A dermoscopic close-up of a skin lesion.
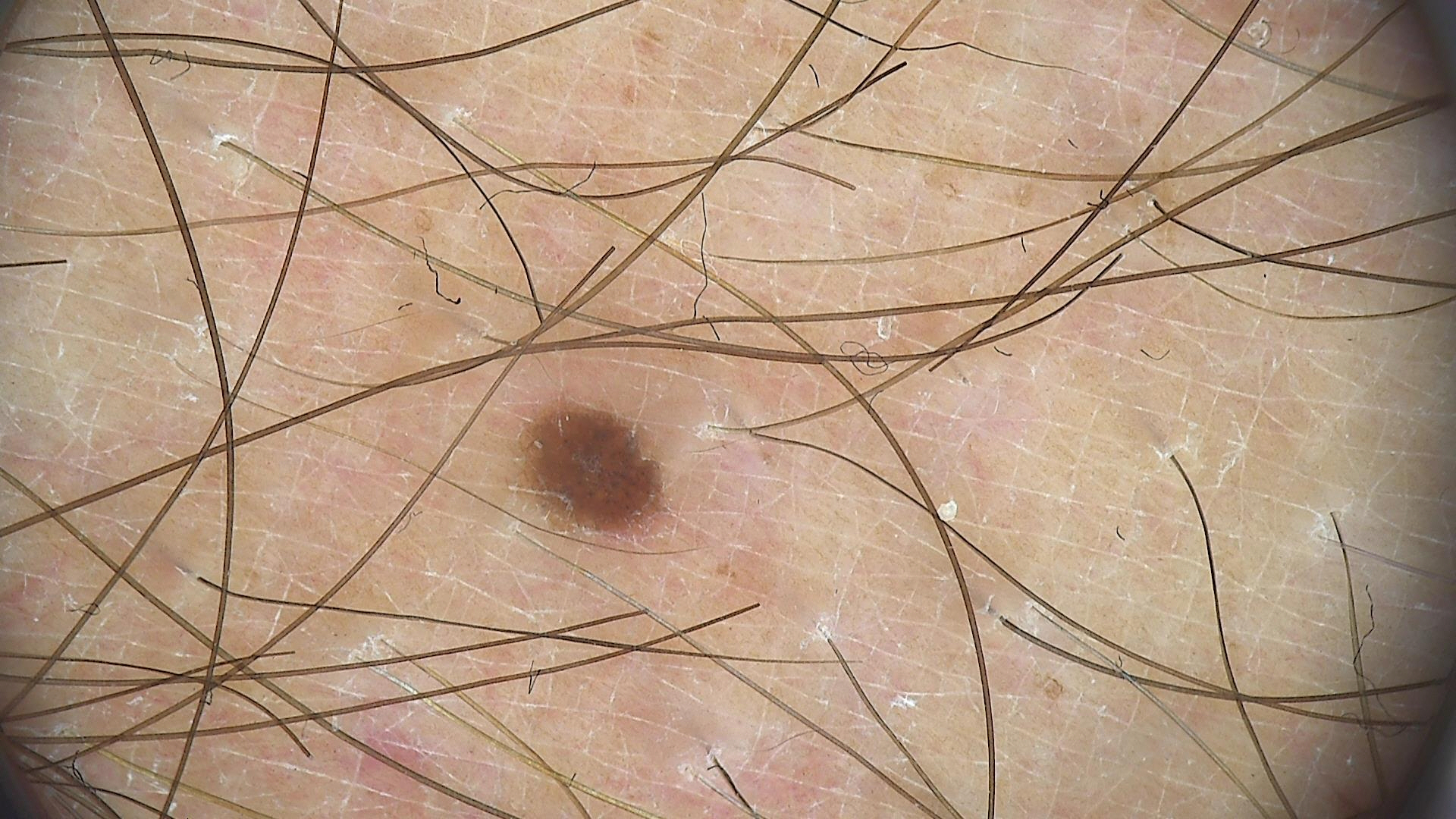Consistent with a benign lesion — a dysplastic junctional nevus.